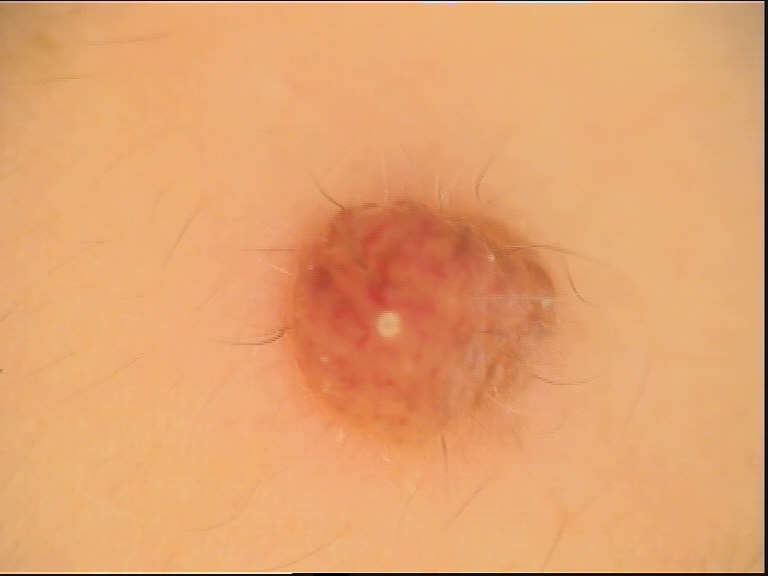image — dermatoscopy | diagnostic label — dermal nevus (expert consensus).